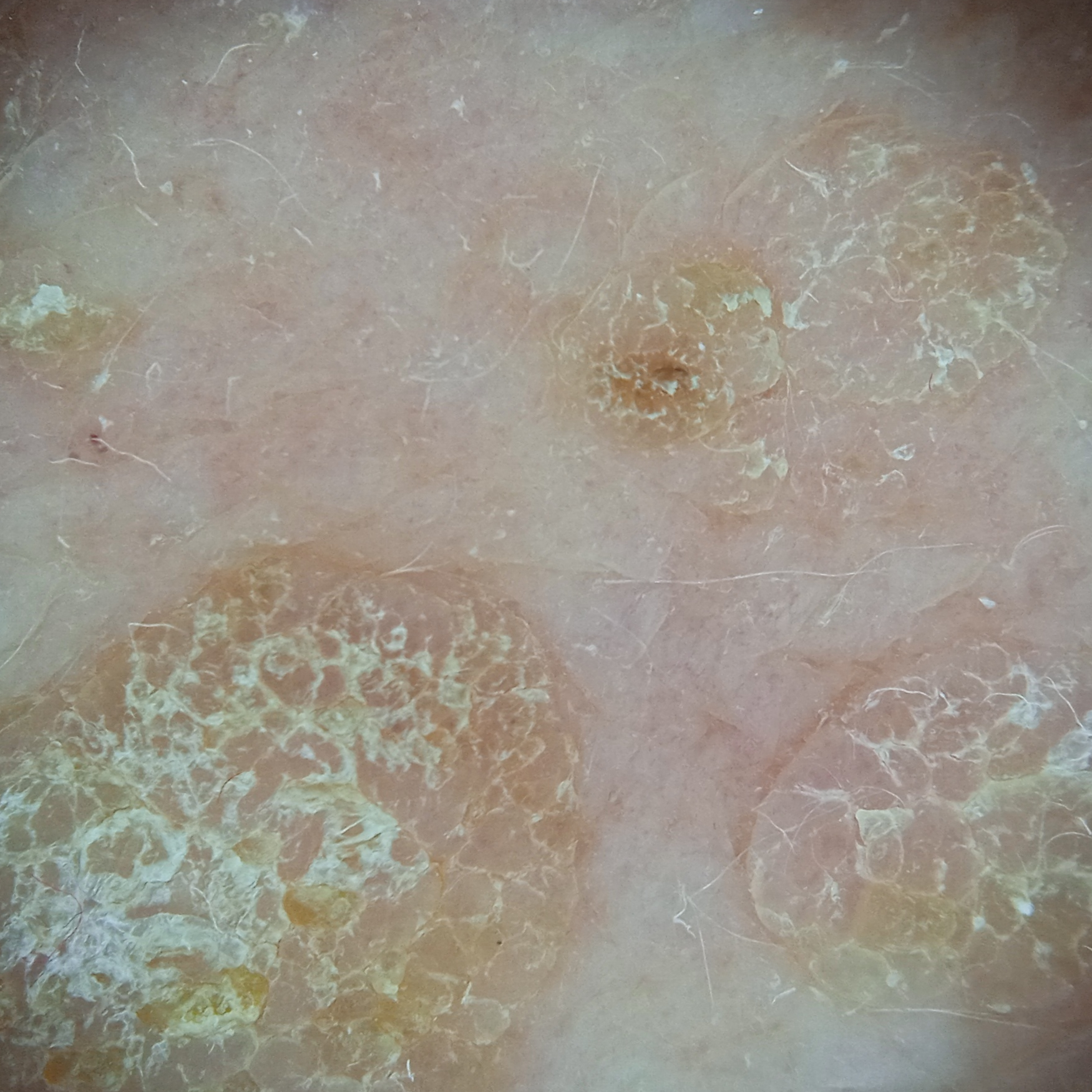A moderate number of moles by the patient's own estimate. Collected as part of a research study, without a referral diagnosis. A dermoscopic image of a skin lesion. The patient says their skin reddens painfully with sun exposure. The lesion is about 10.6 mm across. The lesion was assessed as a seborrheic keratosis.